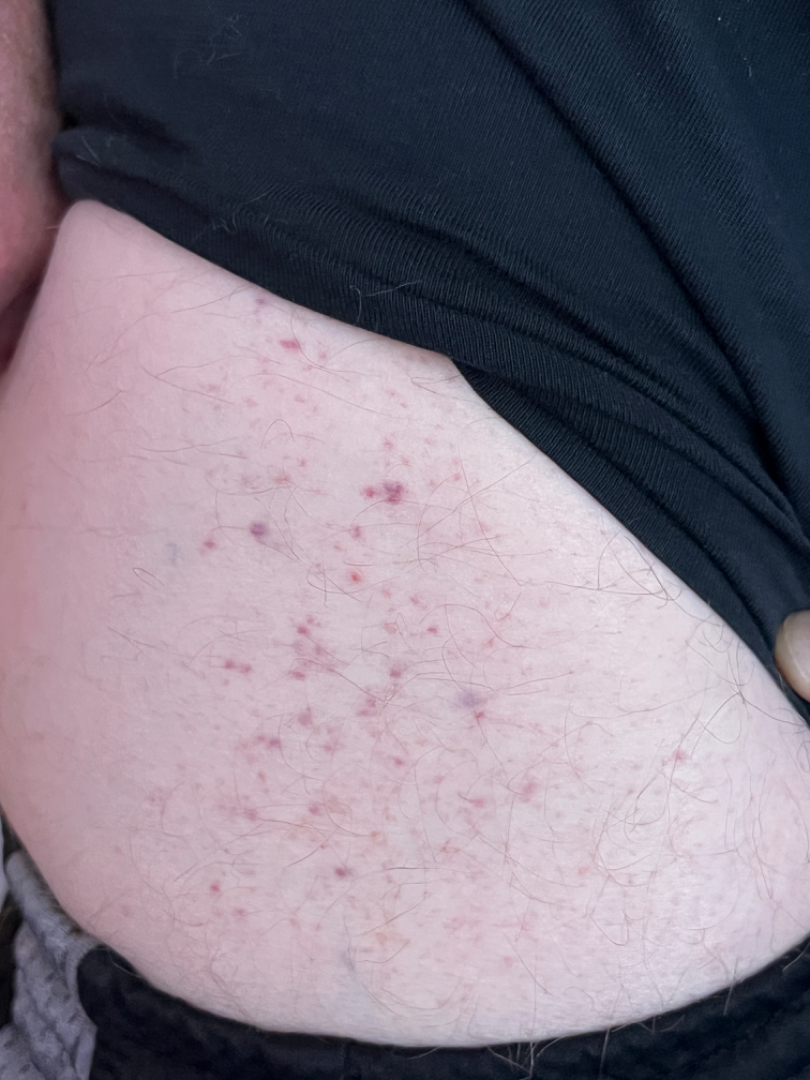The affected area is the leg. A close-up photograph. The patient considered this a rash. The subject is 50–59, male. The patient notes the condition has been present for less than one week. The patient reported no relevant symptoms from the lesion. The lesion is described as flat. The reviewing clinician's impression was: the differential, in no particular order, includes Folliculitis, Hypersensitivity and Leukocytoclastic Vasculitis.